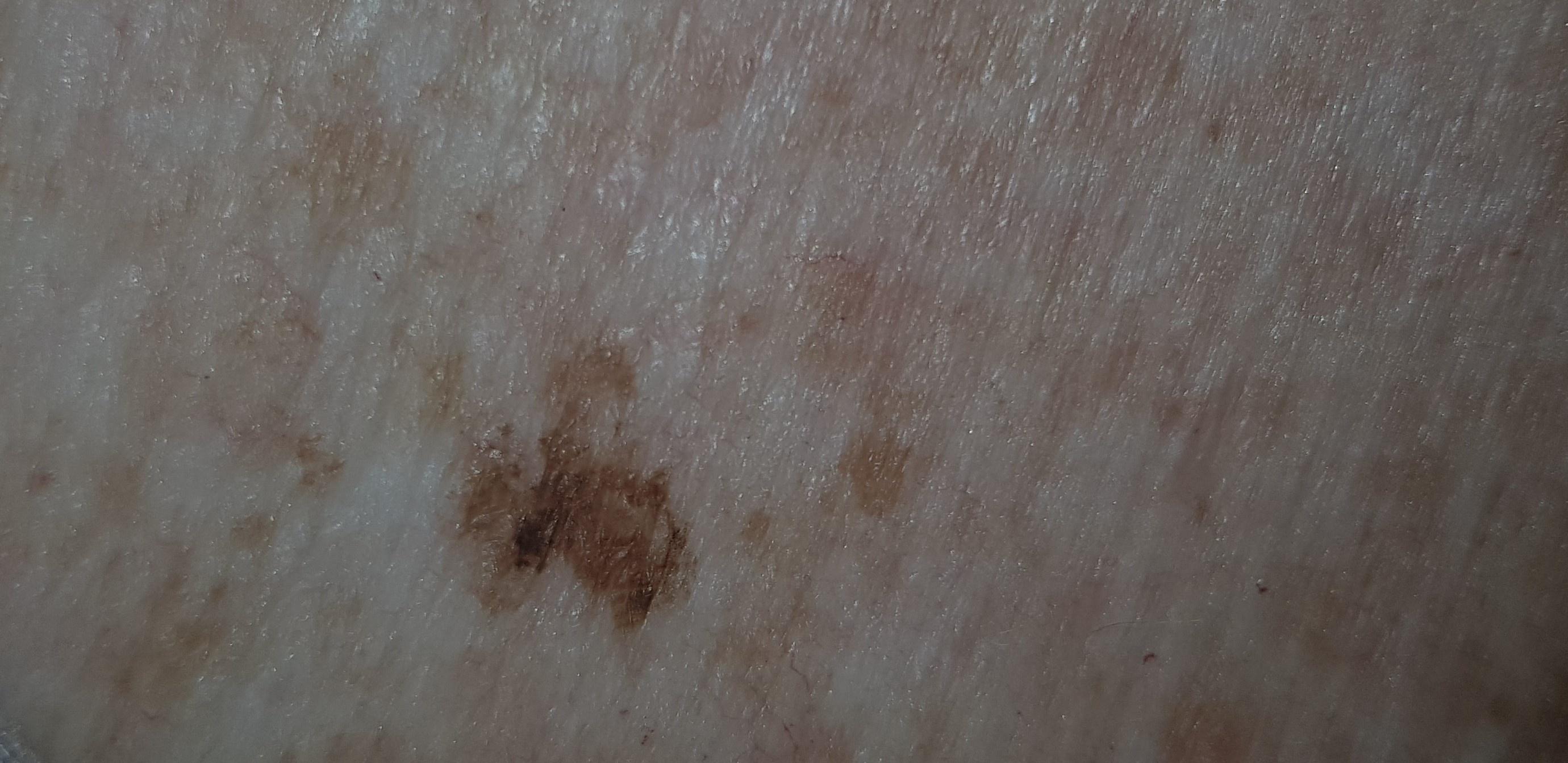Fitzpatrick: II
subject: male, aged 73 to 77
imaging: clinical overview photograph
location: the trunk
diagnostic label: Nevus (biopsy-proven)